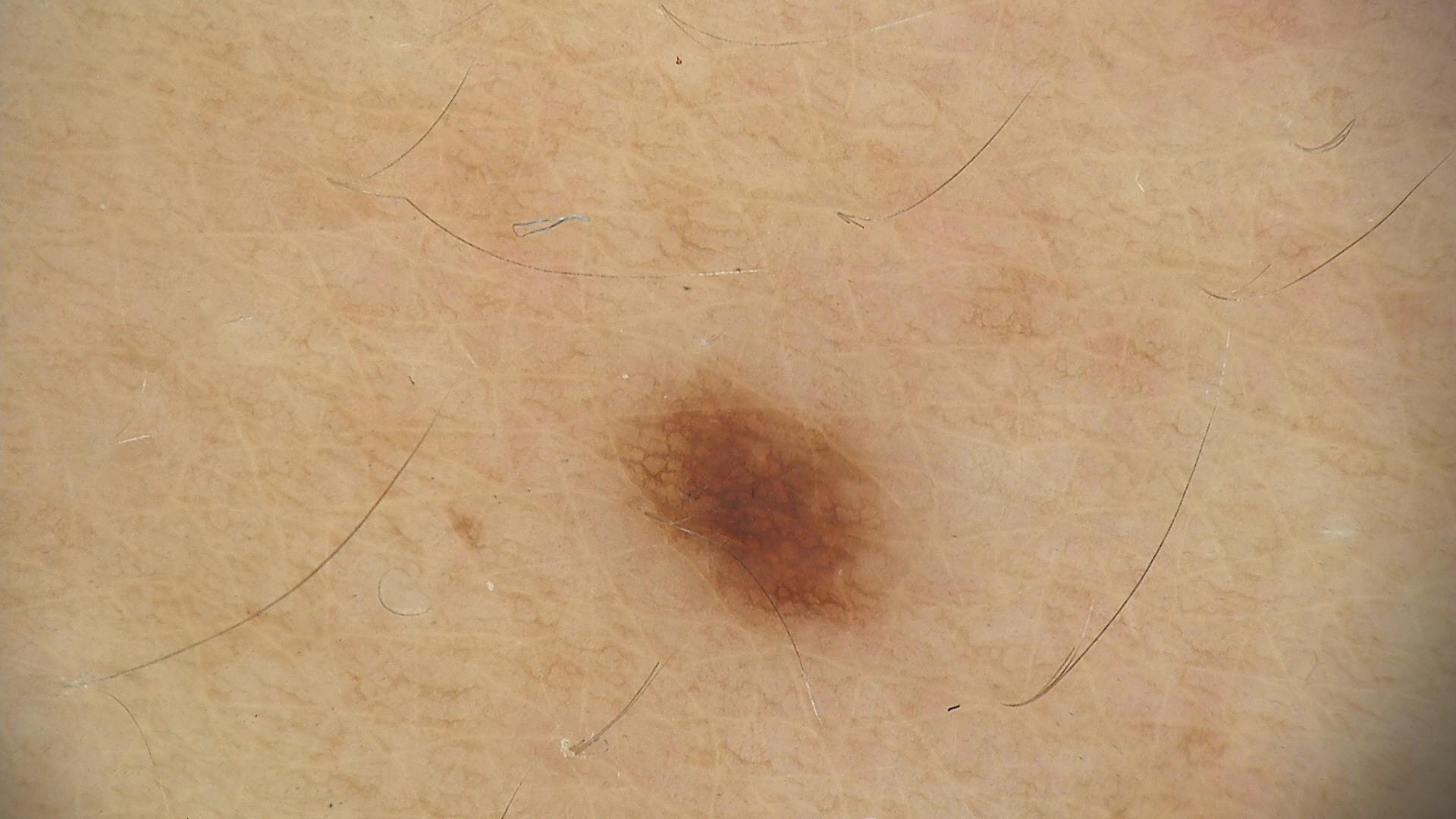label: dysplastic junctional nevus (expert consensus).